The subject is a male about 70 years old; a dermoscopic image of a skin lesion:
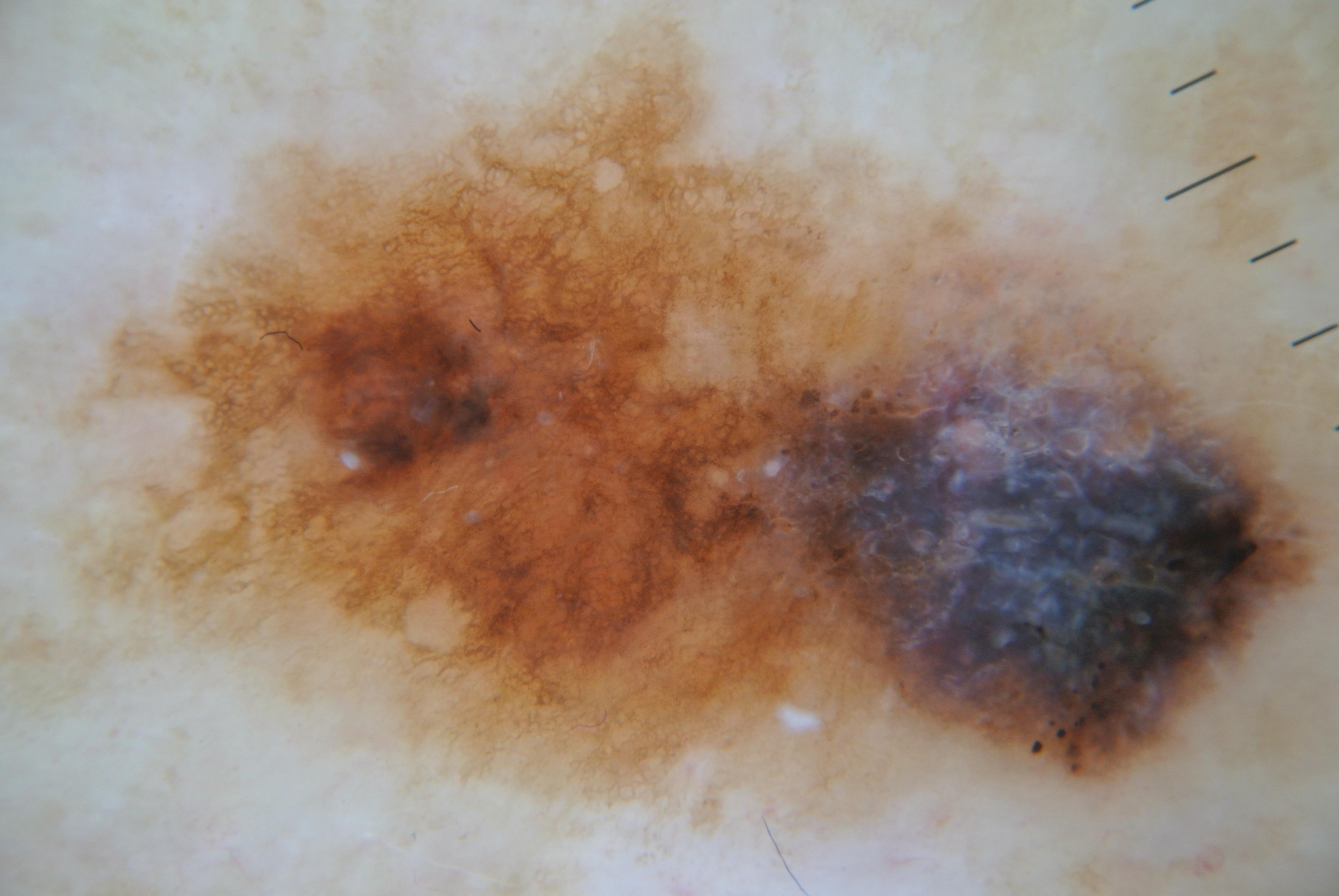Dermoscopic review identifies pigment network; no negative network, streaks, globules, or milia-like cysts.
As (left, top, right, bottom), the lesion is located at [55,15,1330,848].
On biopsy, the diagnosis was a melanoma, a malignant skin lesion.